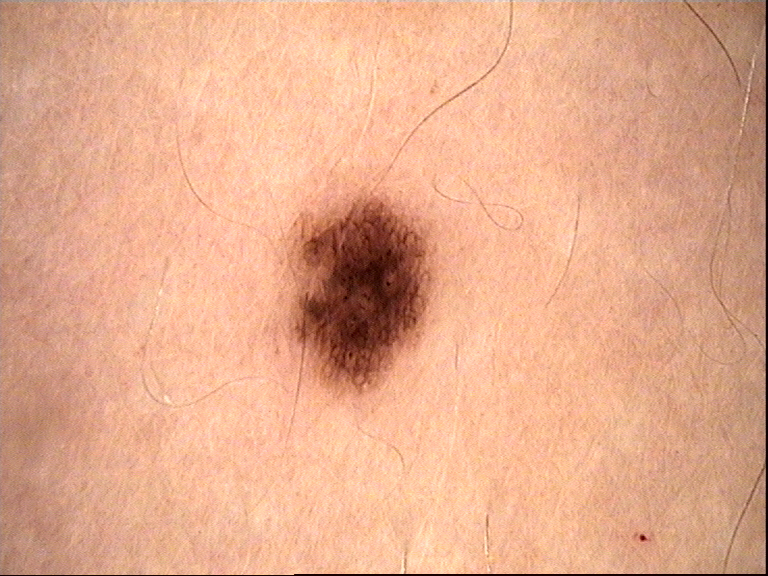The diagnostic label was a dysplastic junctional nevus.